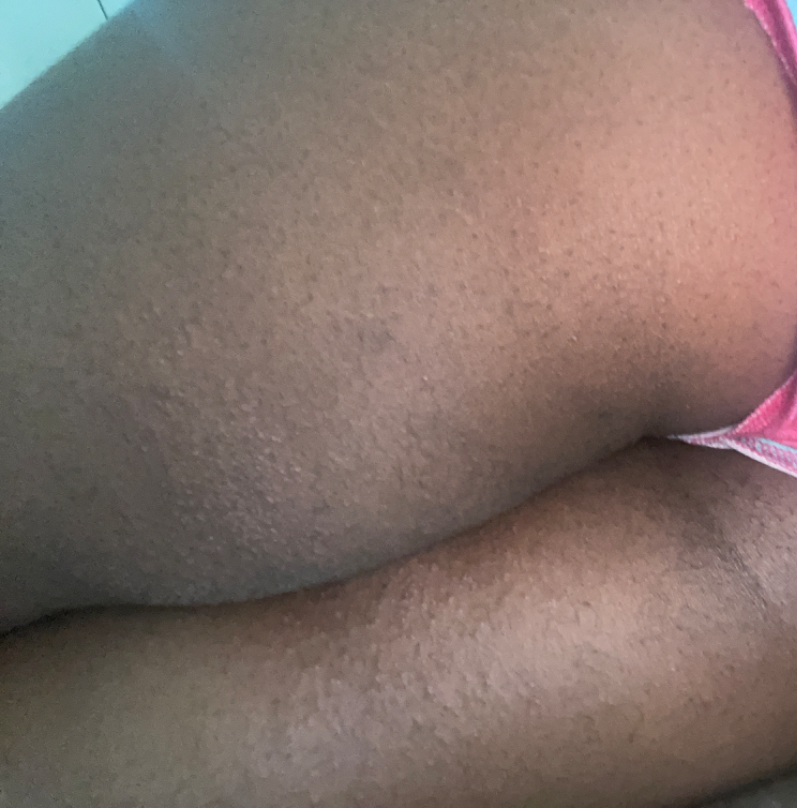Background: The contributor is a female aged 18–29. The photograph was taken at an angle. Findings: The reviewing dermatologists' impression was: most likely Eczema; possibly Folliculitis.